Female subject, age 40–49. The patient notes itching. No constitutional symptoms were reported. The photograph is a close-up of the affected area. The affected area is the arm and leg.
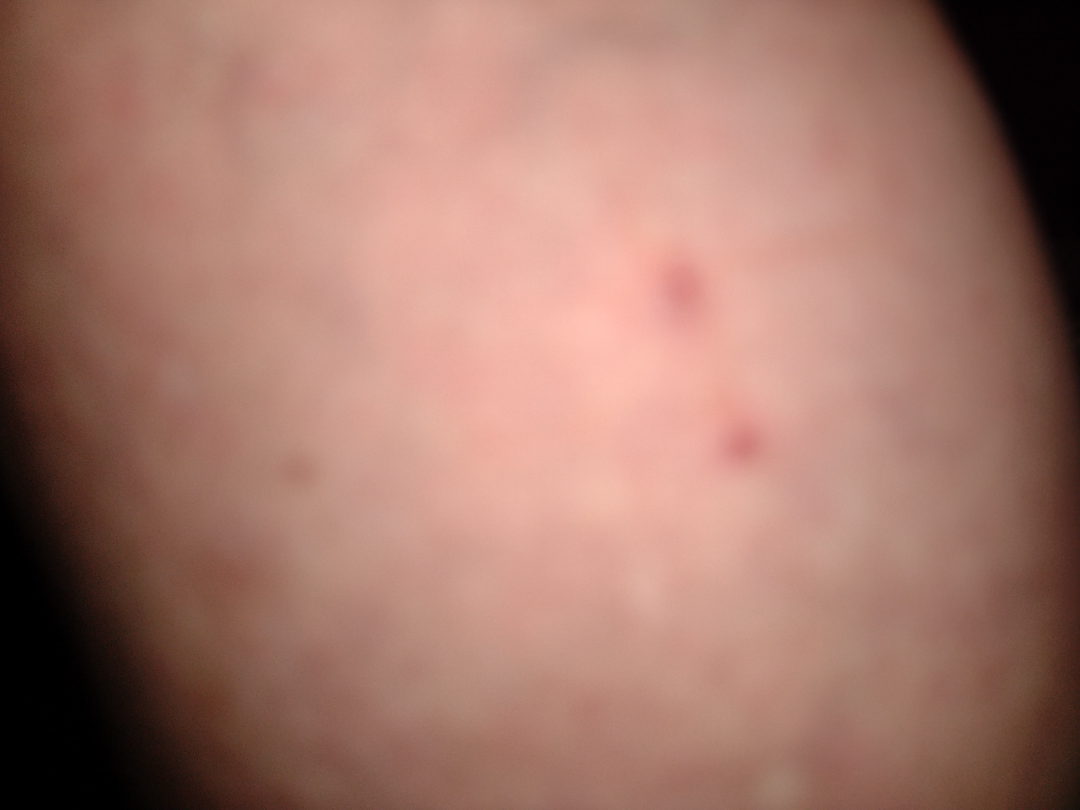Review:
Diagnostic features were not clearly distinguishable in this photograph.